A dermoscopic image of a skin lesion:
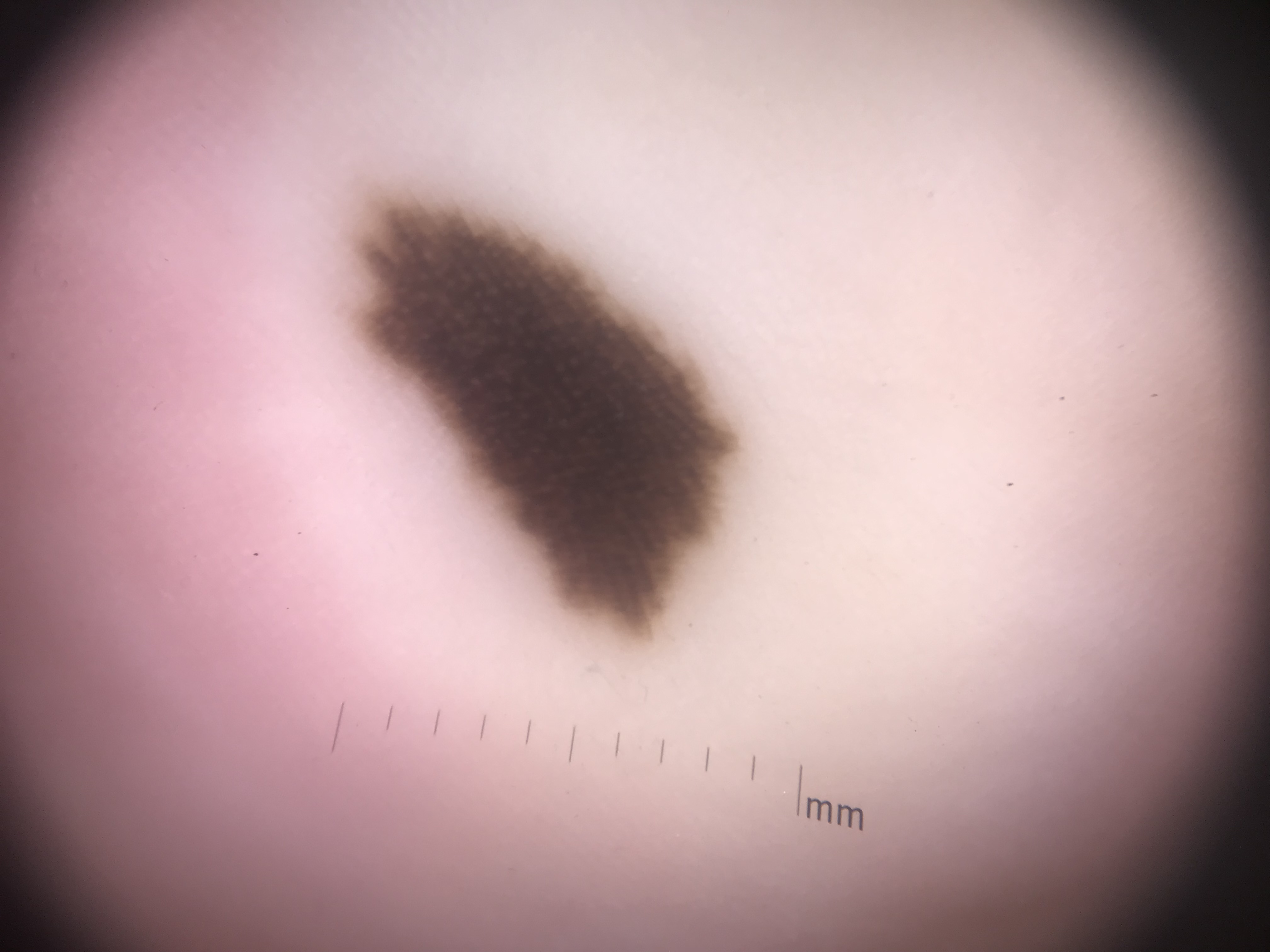Conclusion: The diagnosis was an acral junctional nevus.